Located on the front of the torso. The photo was captured at a distance: 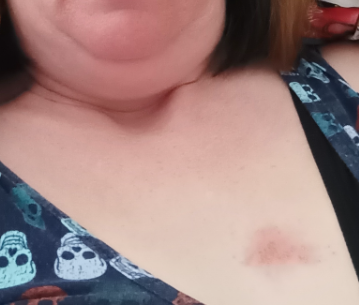Diagnostic features were not clearly distinguishable in this photograph.